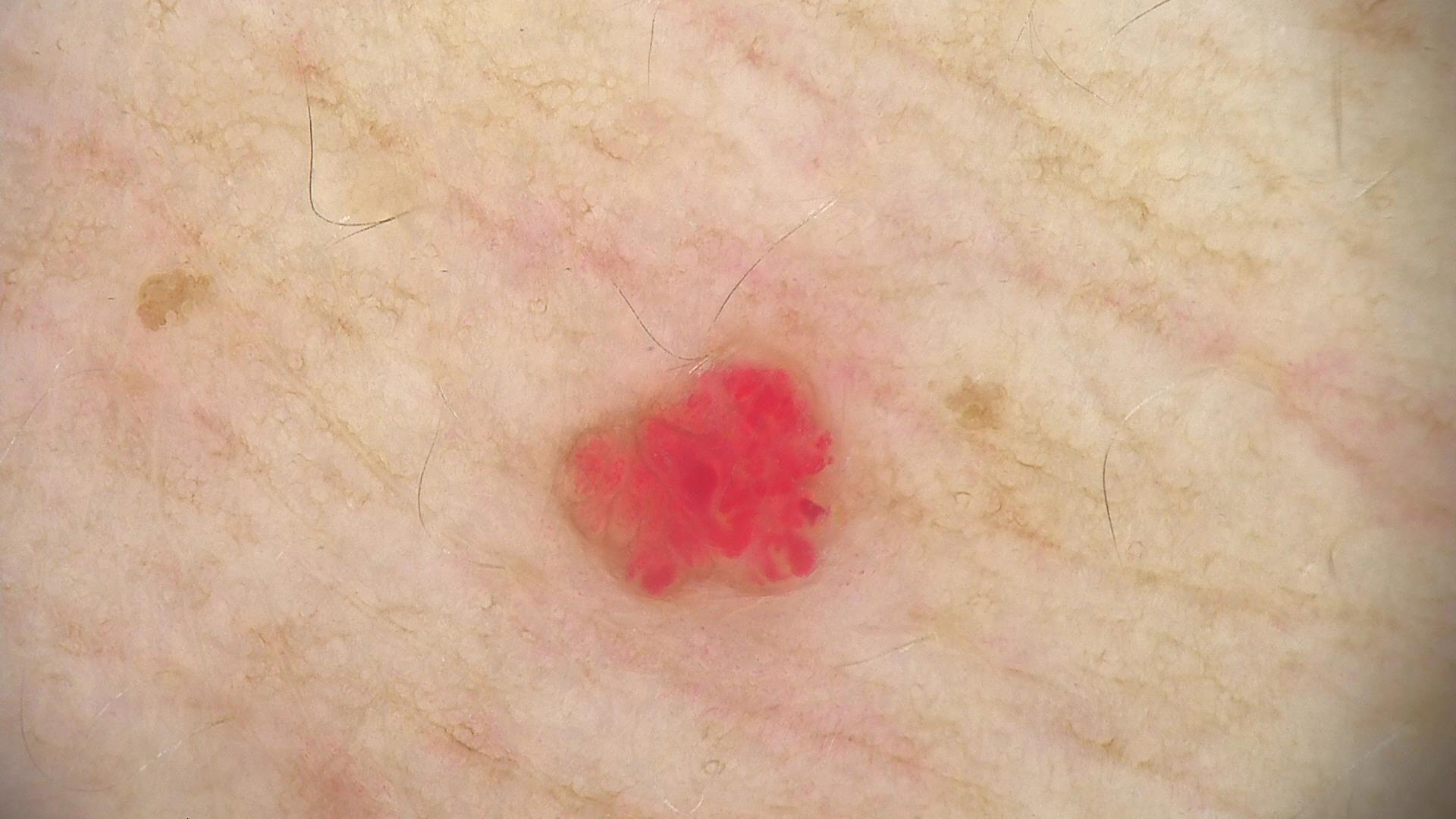image = dermatoscopy
category = vascular
diagnostic label = hemangioma (expert consensus)